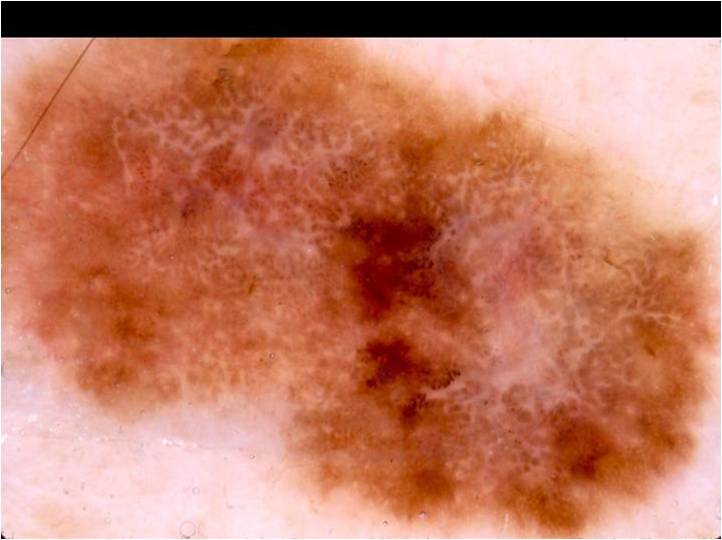A male patient approximately 55 years of age.
A dermoscopic image of a skin lesion.
The lesion spans essentially the entire dermoscopic field.
Dermoscopic review identifies negative network, globules, and pigment network.
Histopathologically confirmed as a melanoma, a malignant skin lesion.